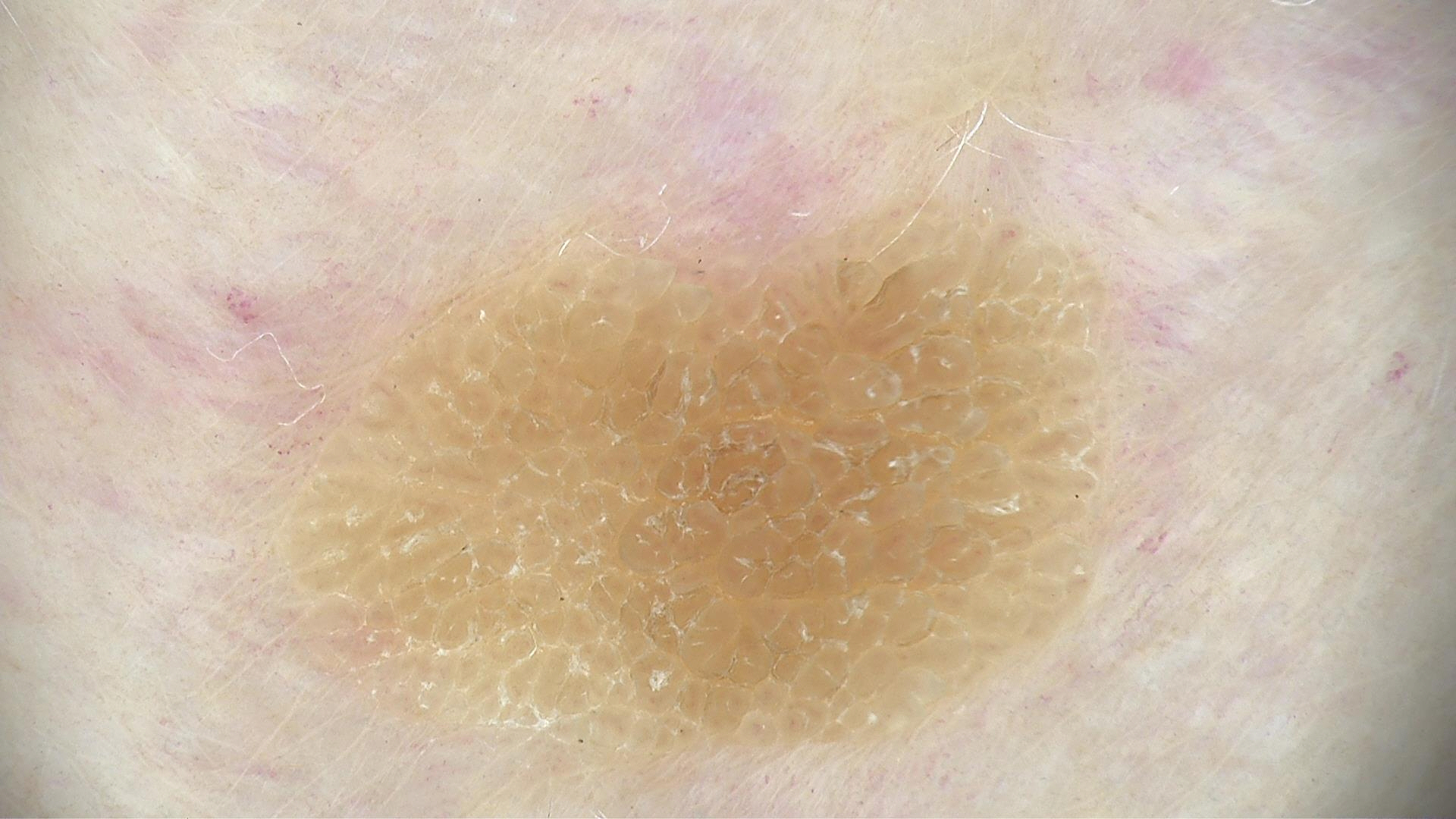Dermoscopy of a skin lesion.
The diagnostic label was a keratinocytic lesion — a seborrheic keratosis.